A male subject 58 years old. Acquired for a research image collection, with no referral diagnosis. A macroscopic clinical photograph of a skin lesion — 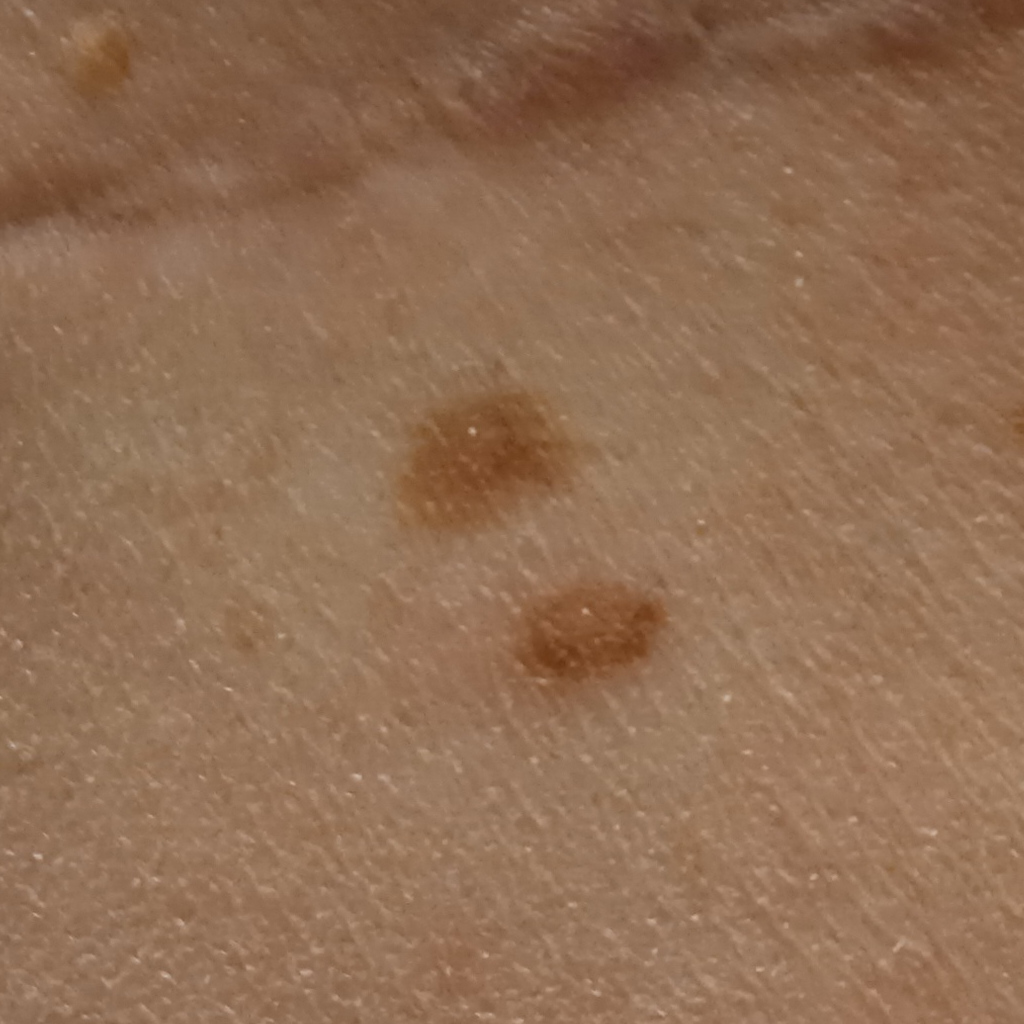Q: Lesion size?
A: 8.6 mm
Q: What was the diagnosis?
A: atypical (dysplastic) nevus — dermatologist consensus